Dermoscopy of a skin lesion. The subject is a female aged 28-32:
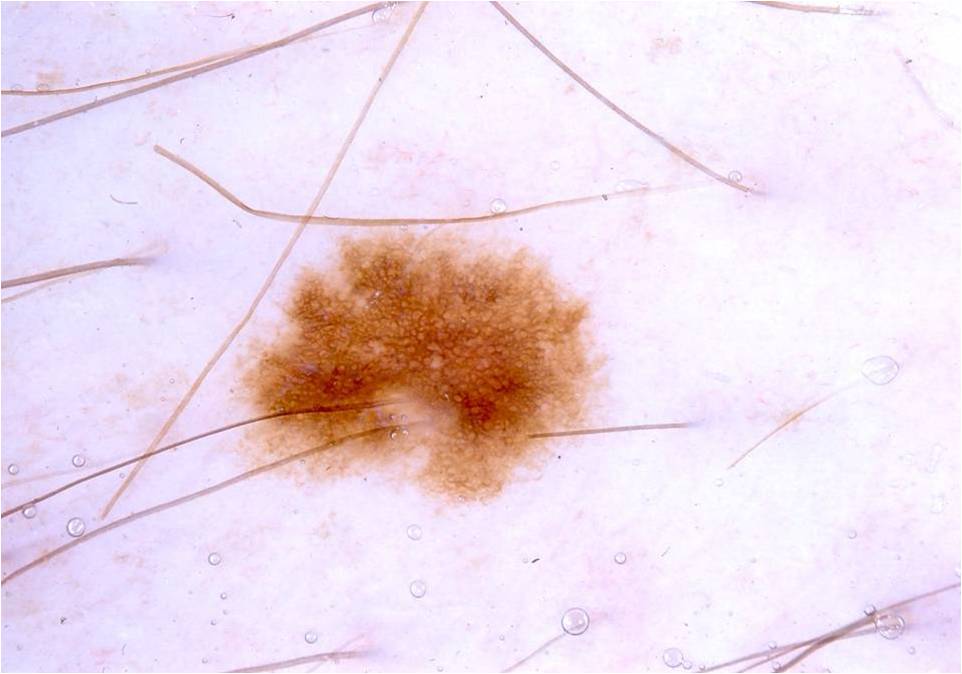The lesion occupies roughly 13% of the field.
The visible lesion spans 231 224 609 515.
The dermoscopic pattern shows pigment network; no milia-like cysts, streaks, negative network, or globules.
The clinical diagnosis was a melanocytic nevus.